A dermoscopic close-up of a skin lesion.
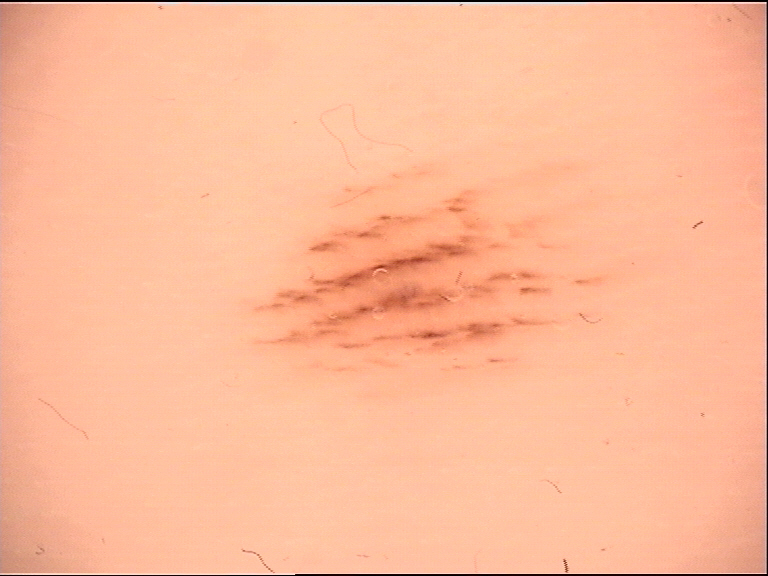Consistent with a banal lesion — an acral junctional nevus.